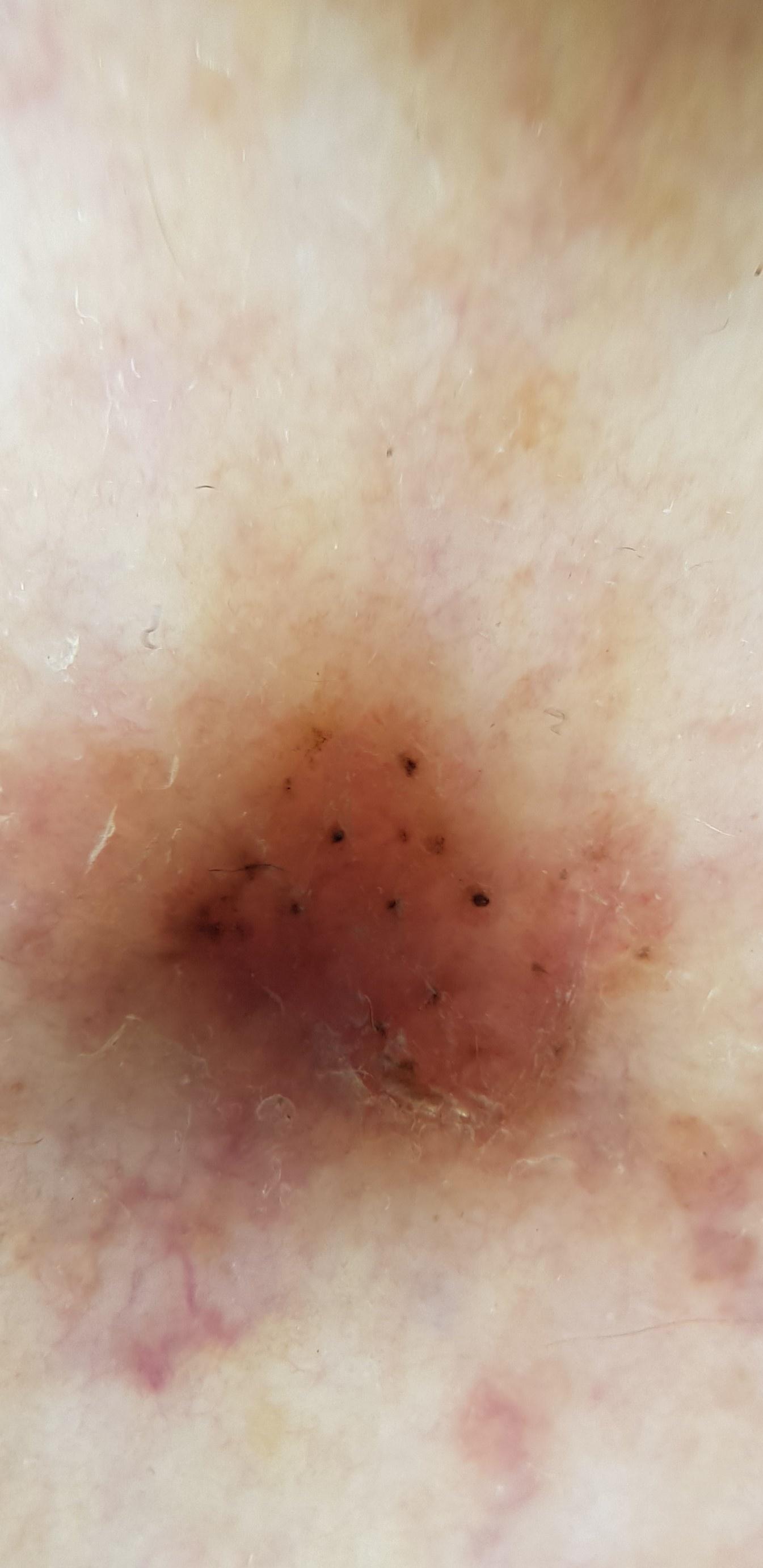A female patient roughly 80 years of age.
The lesion is on a lower extremity.
The biopsy diagnosis was a basal cell carcinoma.